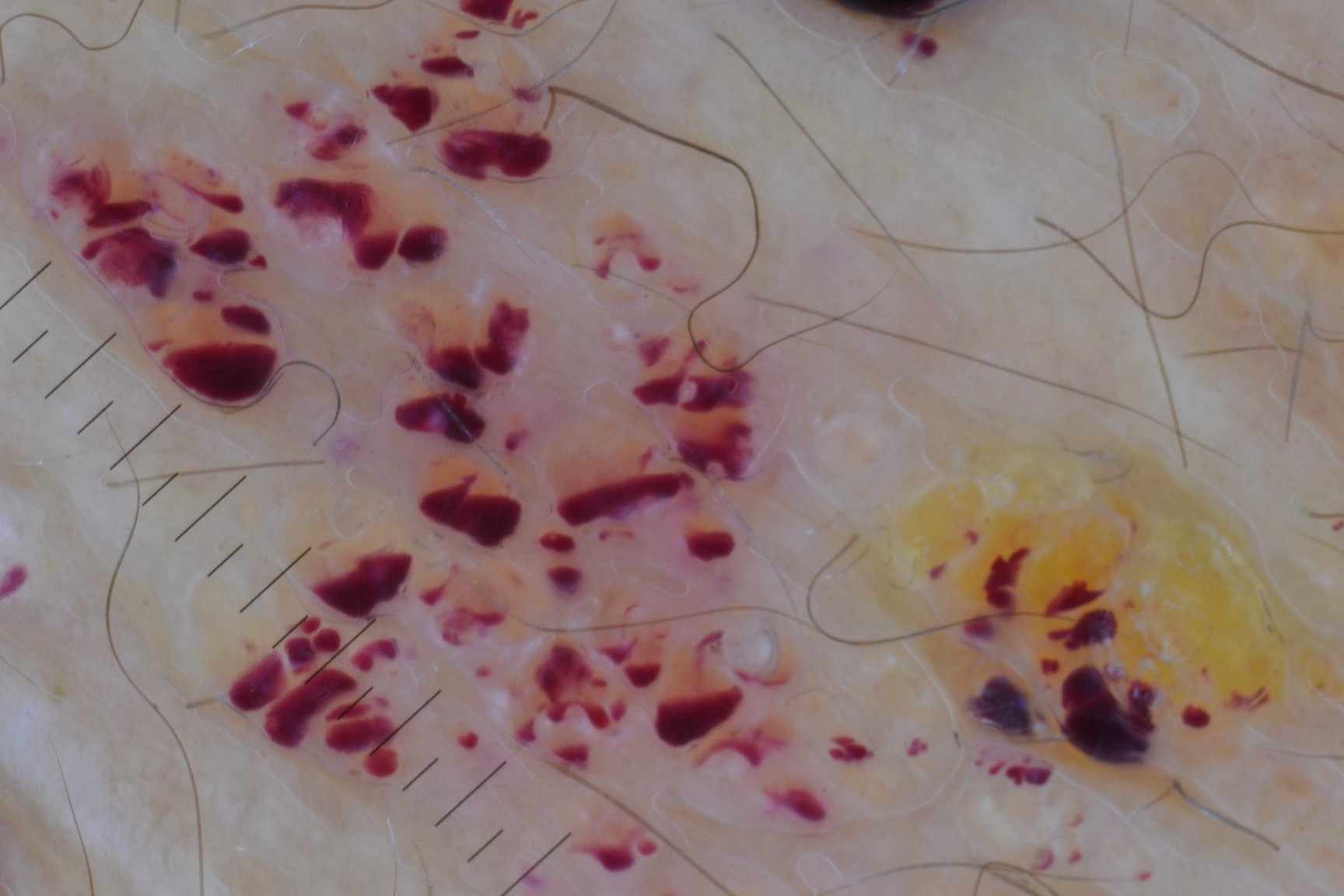Conclusion: The diagnosis was a benign, vascular lesion — a lymphangioma.